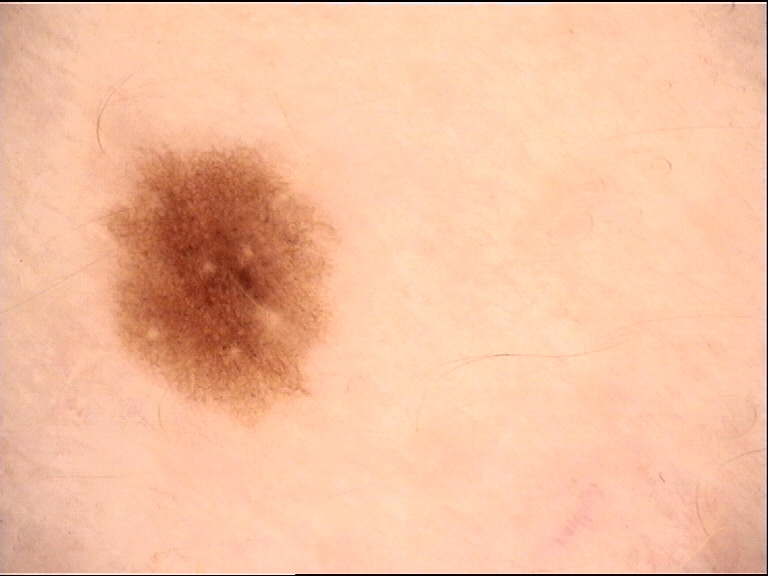Summary:
A dermatoscopic image of a skin lesion.
Conclusion:
The diagnosis was a dysplastic junctional nevus.